A skin lesion imaged with a dermatoscope.
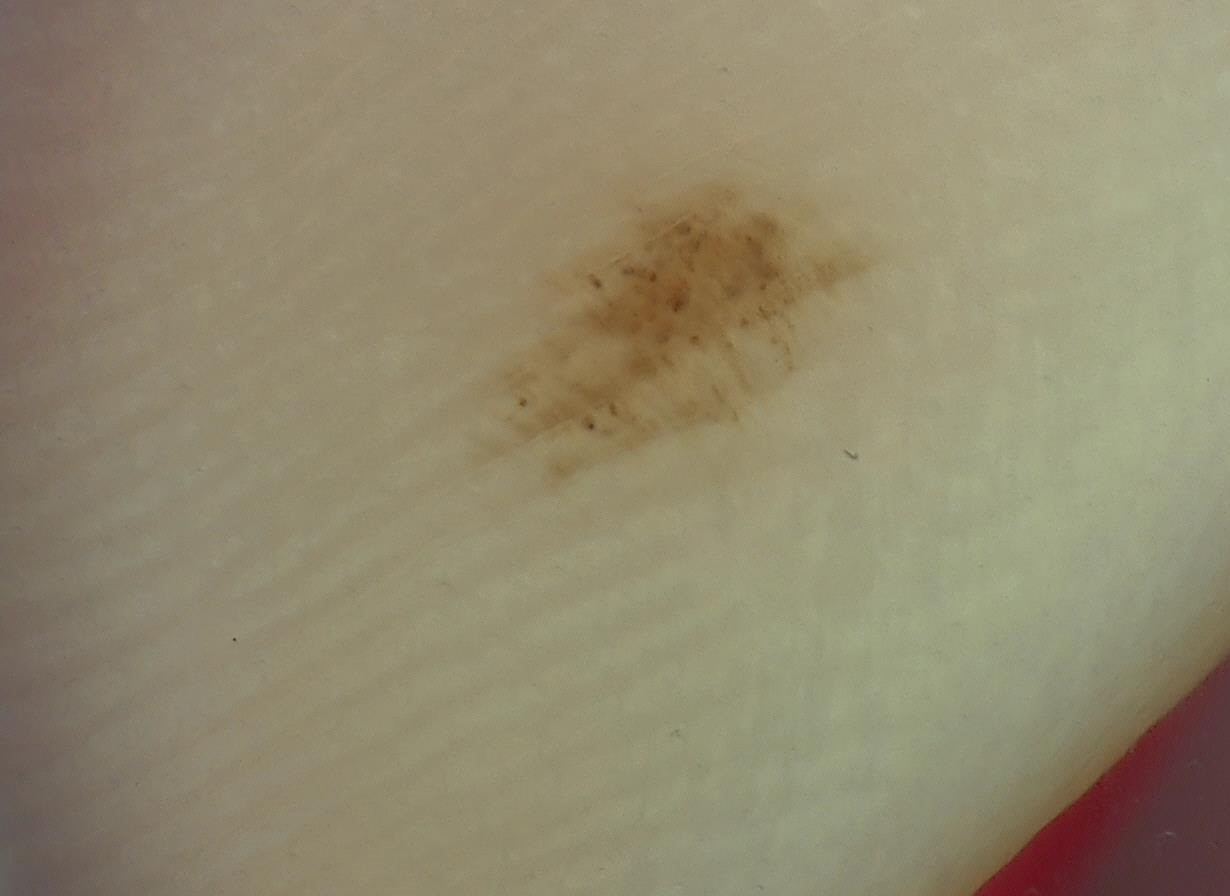Q: What is the diagnosis?
A: acral dysplastic junctional nevus (expert consensus)